A female patient aged around 80 · the chart notes a prior melanoma and a first-degree relative with melanoma · a clinical overview photograph of a skin lesion · recorded as skin type I: 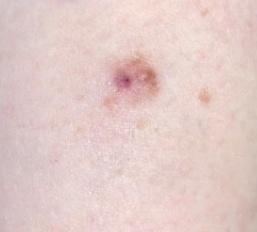Located on a lower extremity. Biopsy-confirmed as a skin cancer — a melanoma.